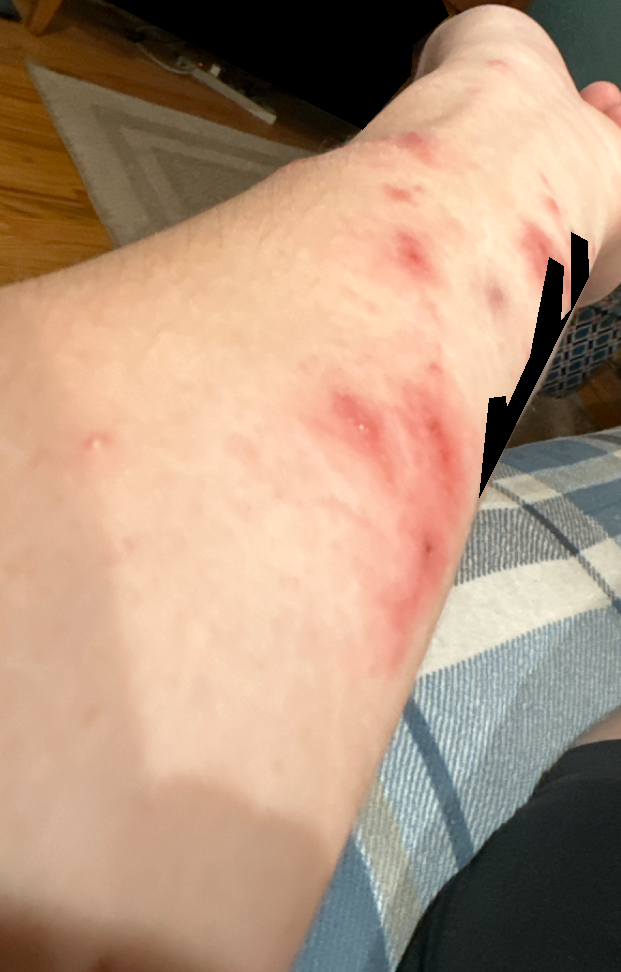One reviewing dermatologist: favoring Allergic Contact Dermatitis; possibly Bullous dermatosis; with consideration of Deep fungal infection.